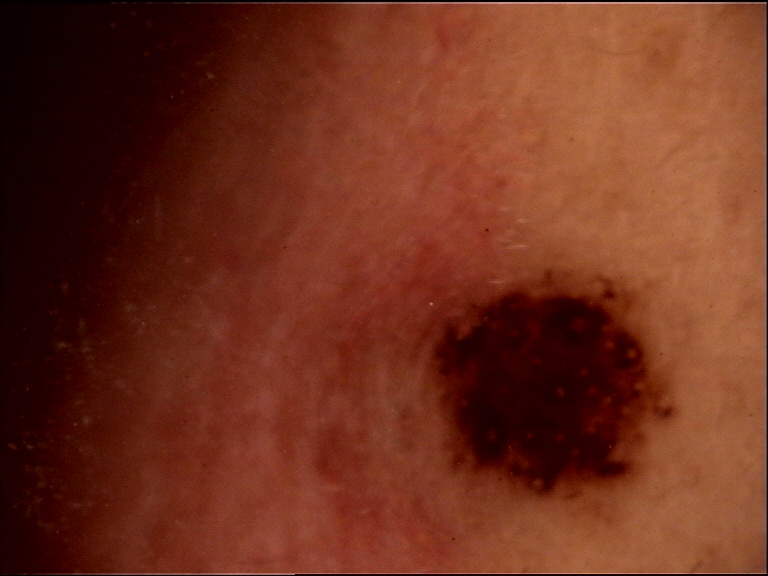Findings:
* classification: banal
* label: congenital compound nevus (expert consensus)